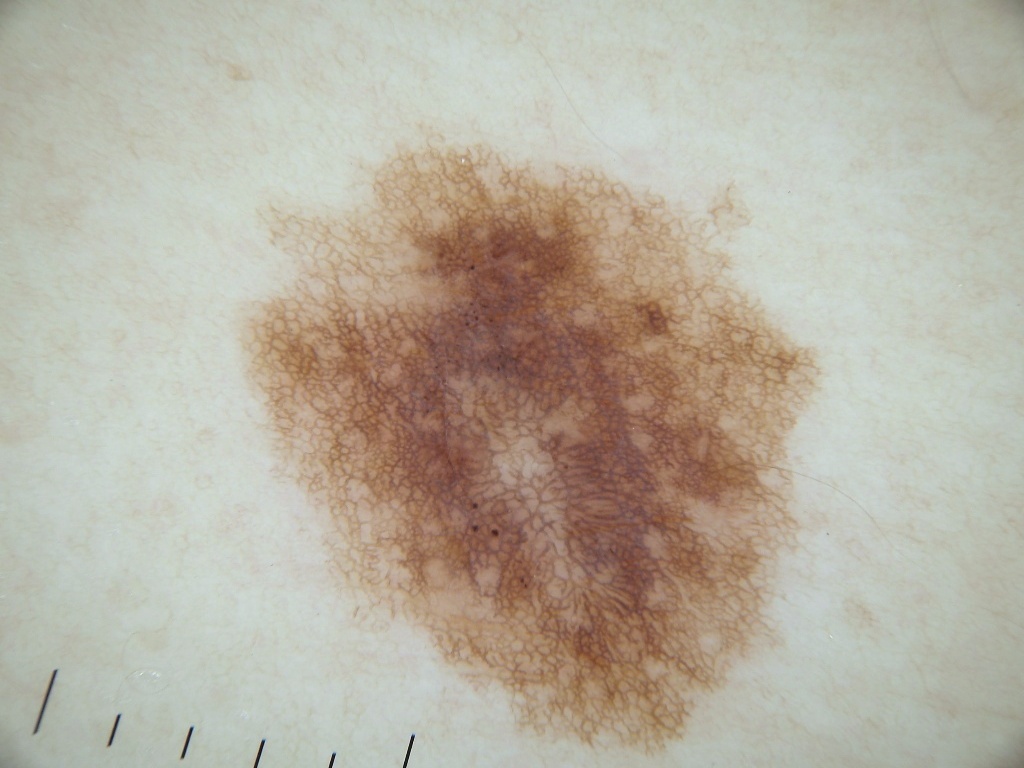Findings:
* image — dermoscopic image
* patient — female, aged 48 to 52
* features — pigment network and globules; absent: streaks, milia-like cysts, and negative network
* lesion bbox — box(222, 115, 837, 765)
* assessment — a melanocytic nevus, a benign skin lesion